Dermoscopy of a skin lesion.
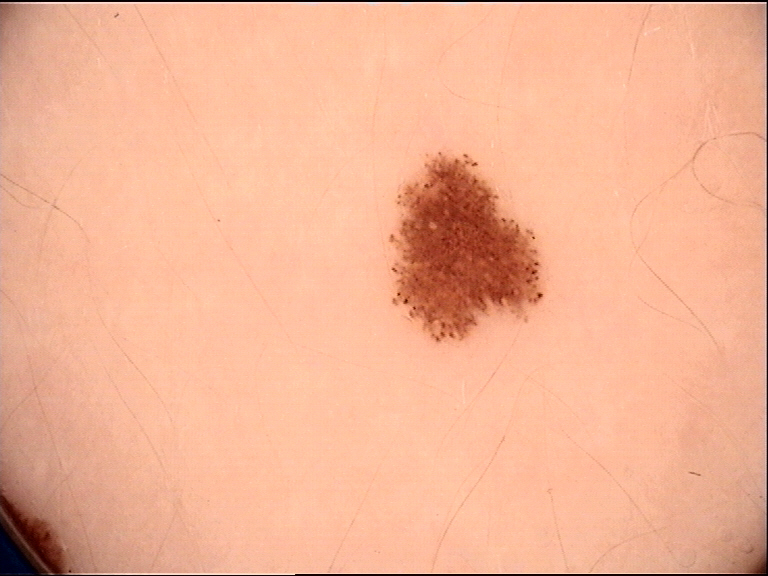This is a banal lesion.
Classified as a junctional nevus.